The photograph is a close-up of the affected area: 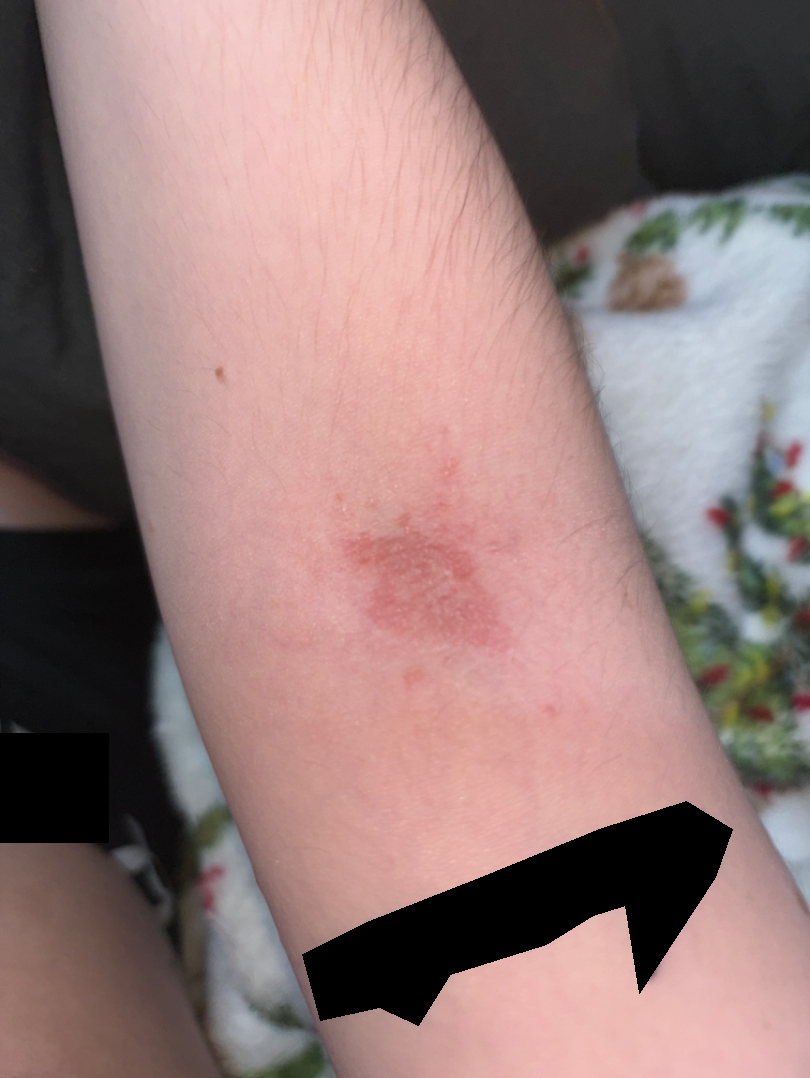On photographic review, in keeping with Eczema.